This is a dermoscopic photograph of a skin lesion, the subject is a male approximately 75 years of age:
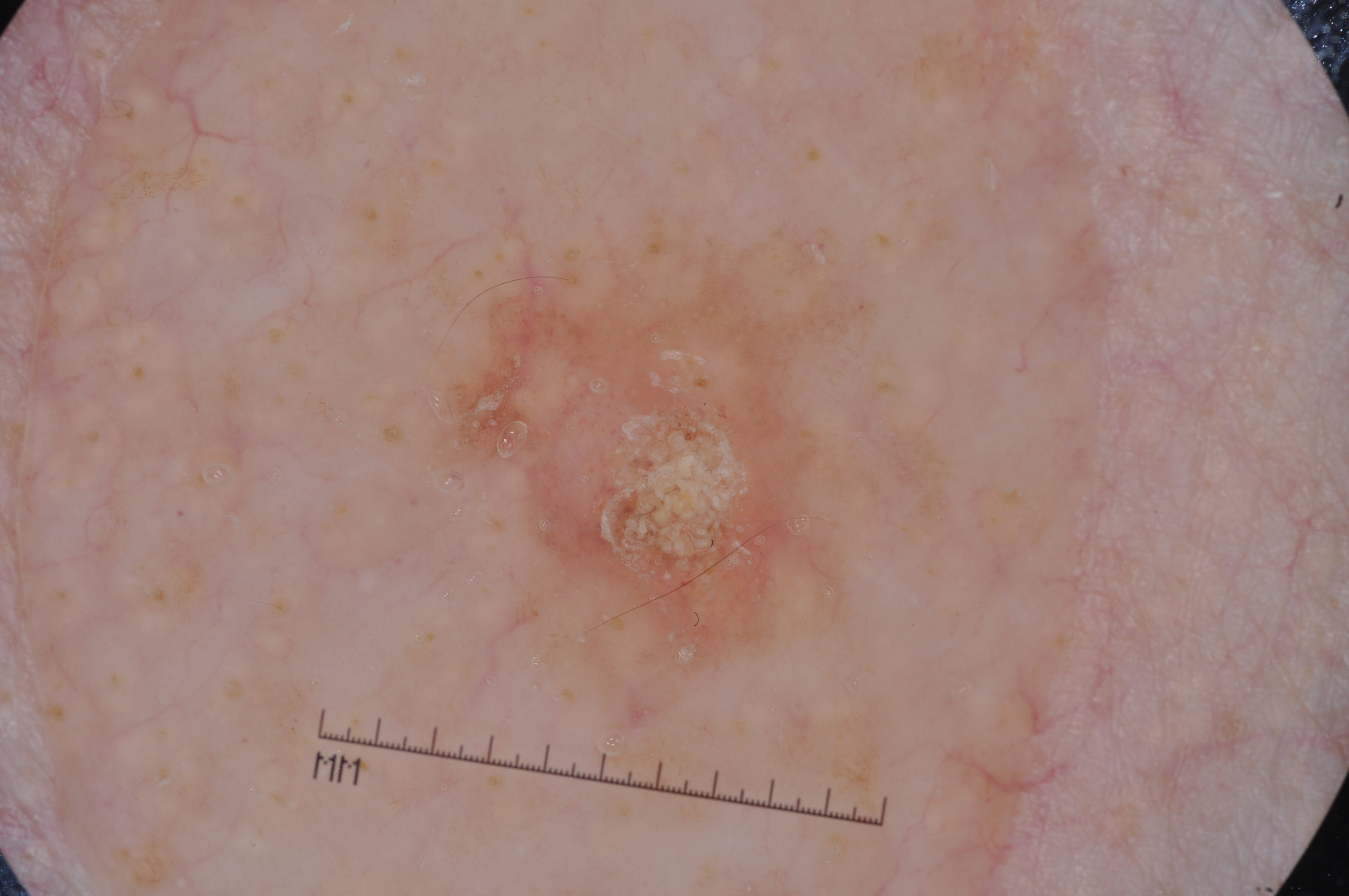Summary:
The visible lesion spans x1=443, y1=224, x2=864, y2=679. Dermoscopically, the lesion shows milia-like cysts.
Conclusion:
Clinically diagnosed as a seborrheic keratosis, a lesion of keratinocytic origin.